A dermoscopic close-up of a skin lesion.
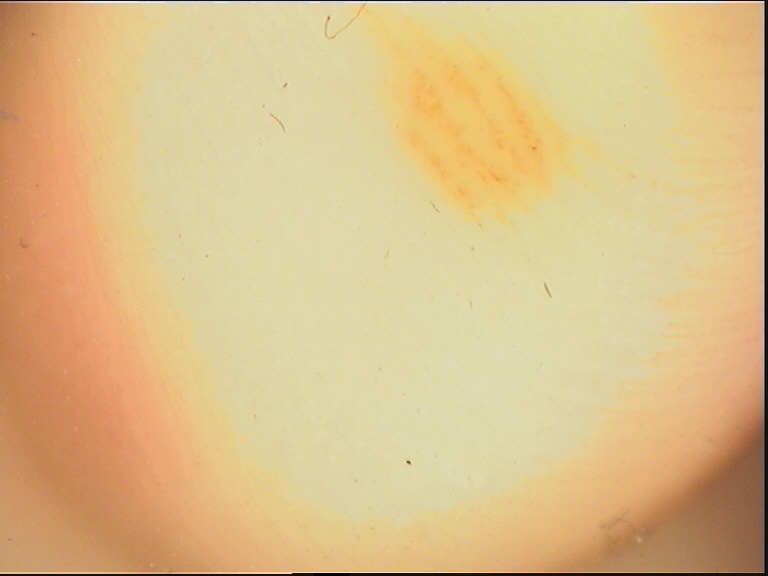The diagnostic label was a banal lesion — an acral junctional nevus.